This is a dermoscopic photograph of a skin lesion. A male subject in their 50s.
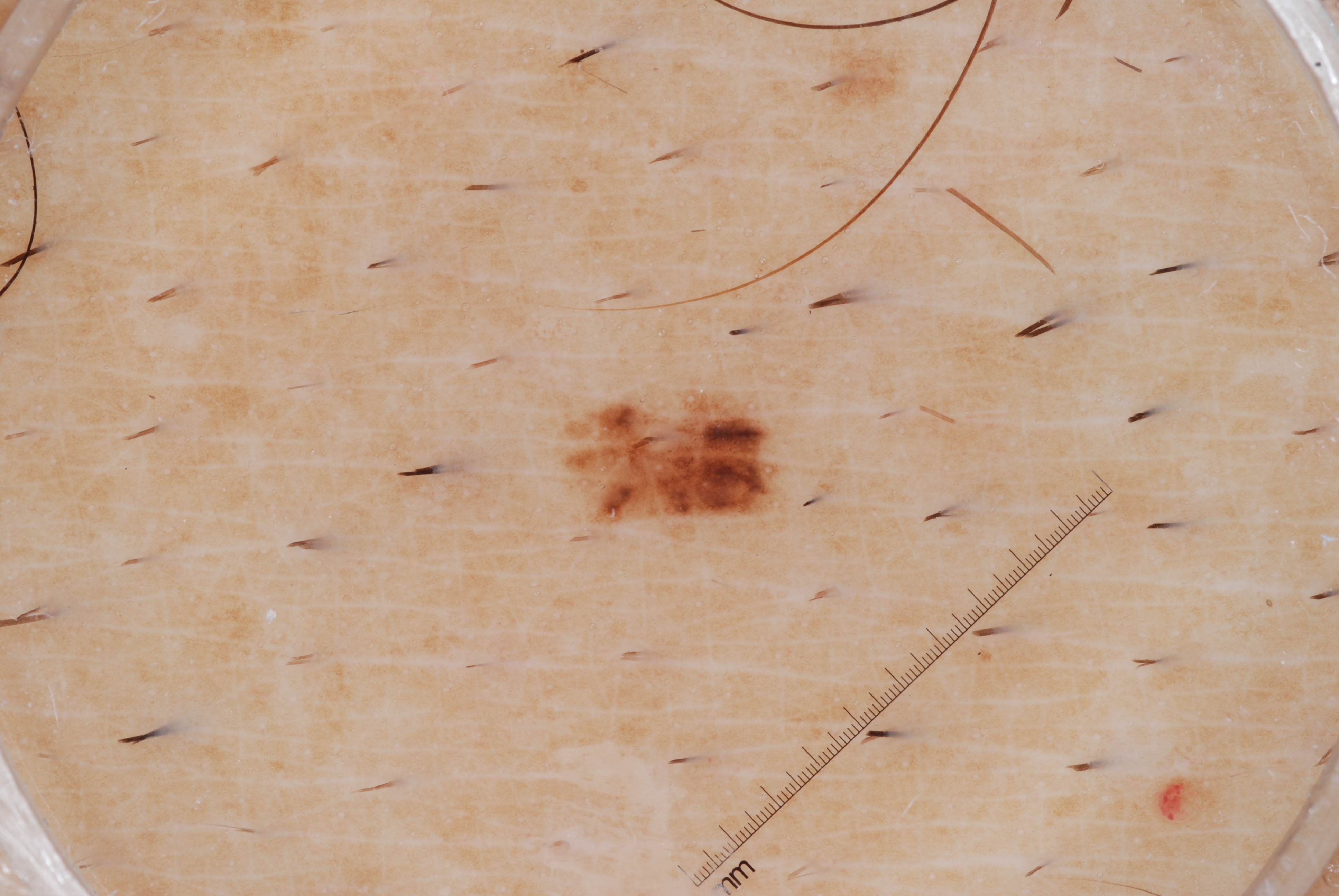Q: What is the lesion's bounding box?
A: x1=575 y1=399 x2=764 y2=518
Q: Which dermoscopic features were noted?
A: milia-like cysts; absent: pigment network, streaks, and negative network
Q: How much of the field does the lesion occupy?
A: ~2% of the field
Q: What is this lesion?
A: a melanocytic nevus, a benign lesion